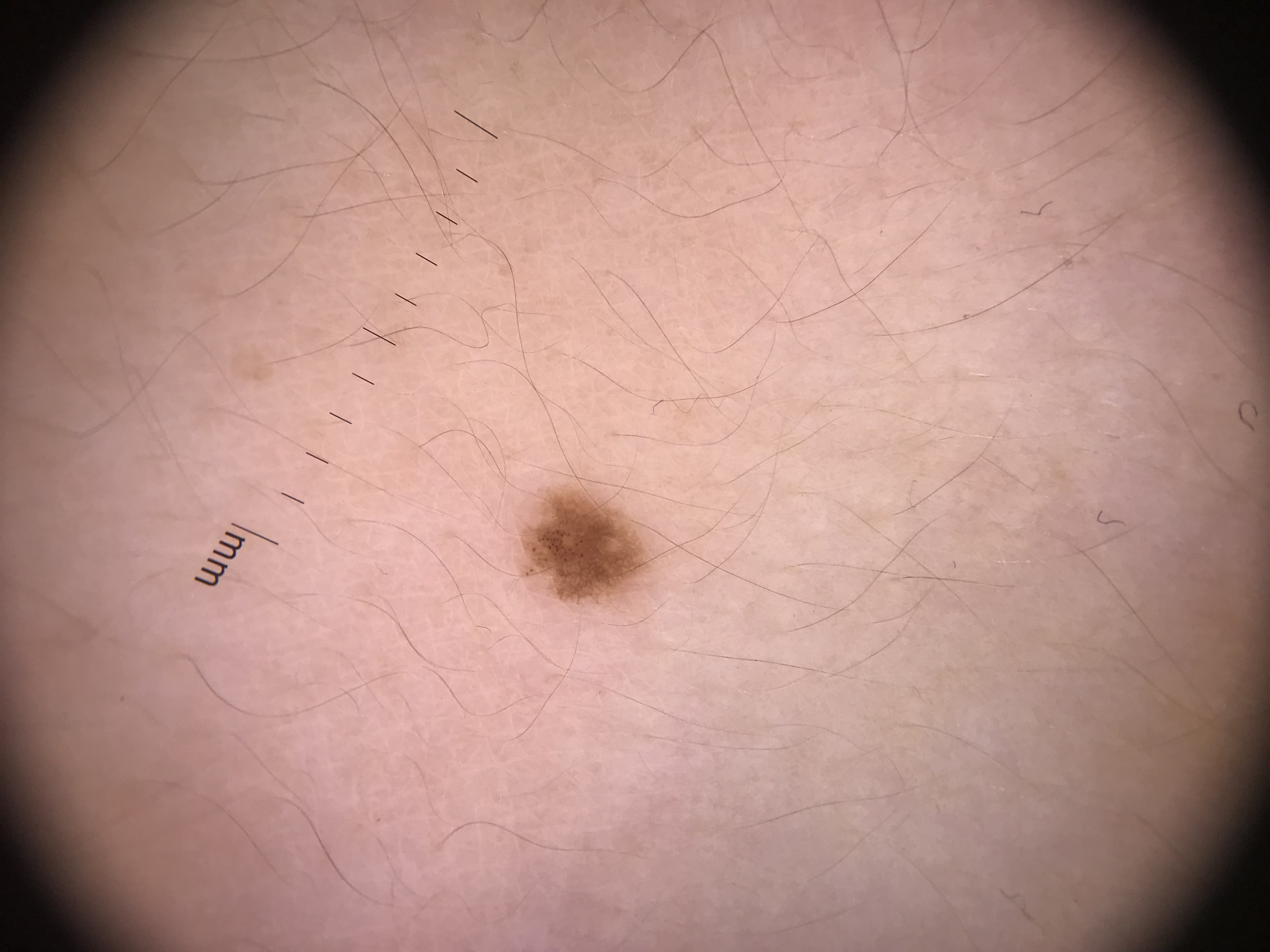A dermatoscopic image of a skin lesion. The diagnosis was a dysplastic junctional nevus.